Reported duration is one to four weeks. Symptoms reported: pain, burning and itching. The lesion is described as raised or bumpy, rough or flaky and fluid-filled. An image taken at a distance. Fitzpatrick skin type II; non-clinician graders estimated MST 2–3. The patient described the issue as a rash. The contributor is a female aged 18–29. The lesion involves the palm.
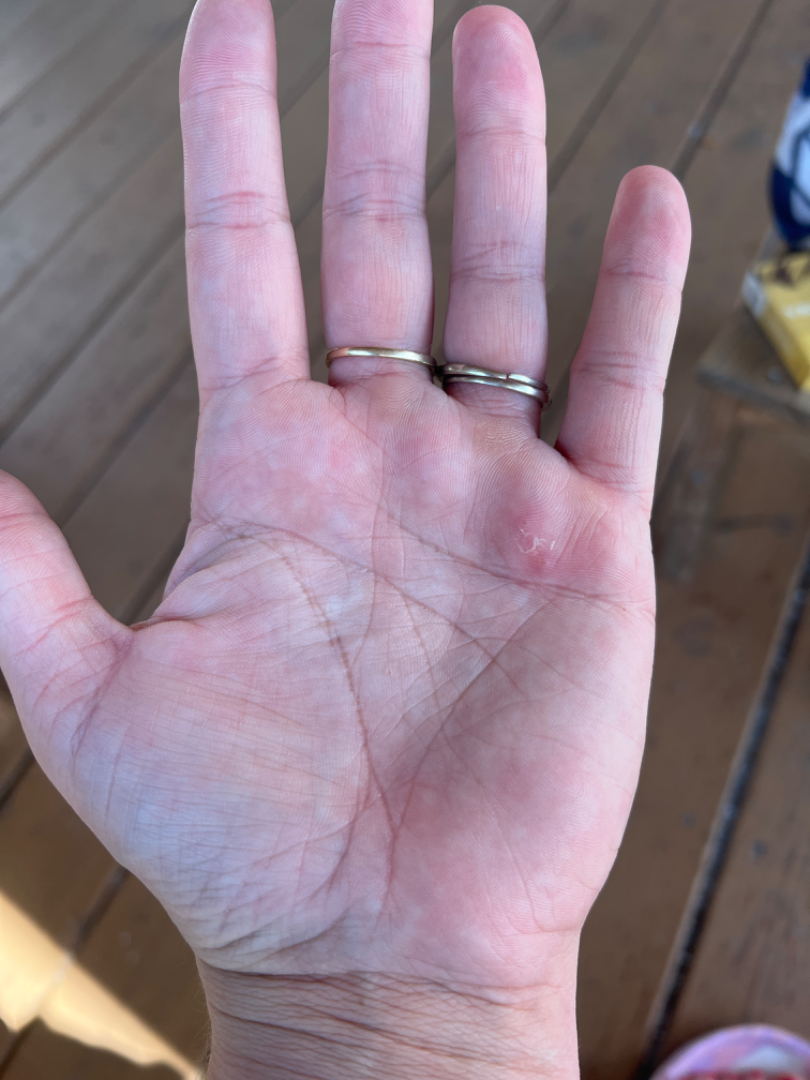  differential:
    leading:
      - Clavus
    considered:
      - Impetigo
      - Foreign body
      - Herpes Simplex